A dermatoscopic image of a skin lesion.
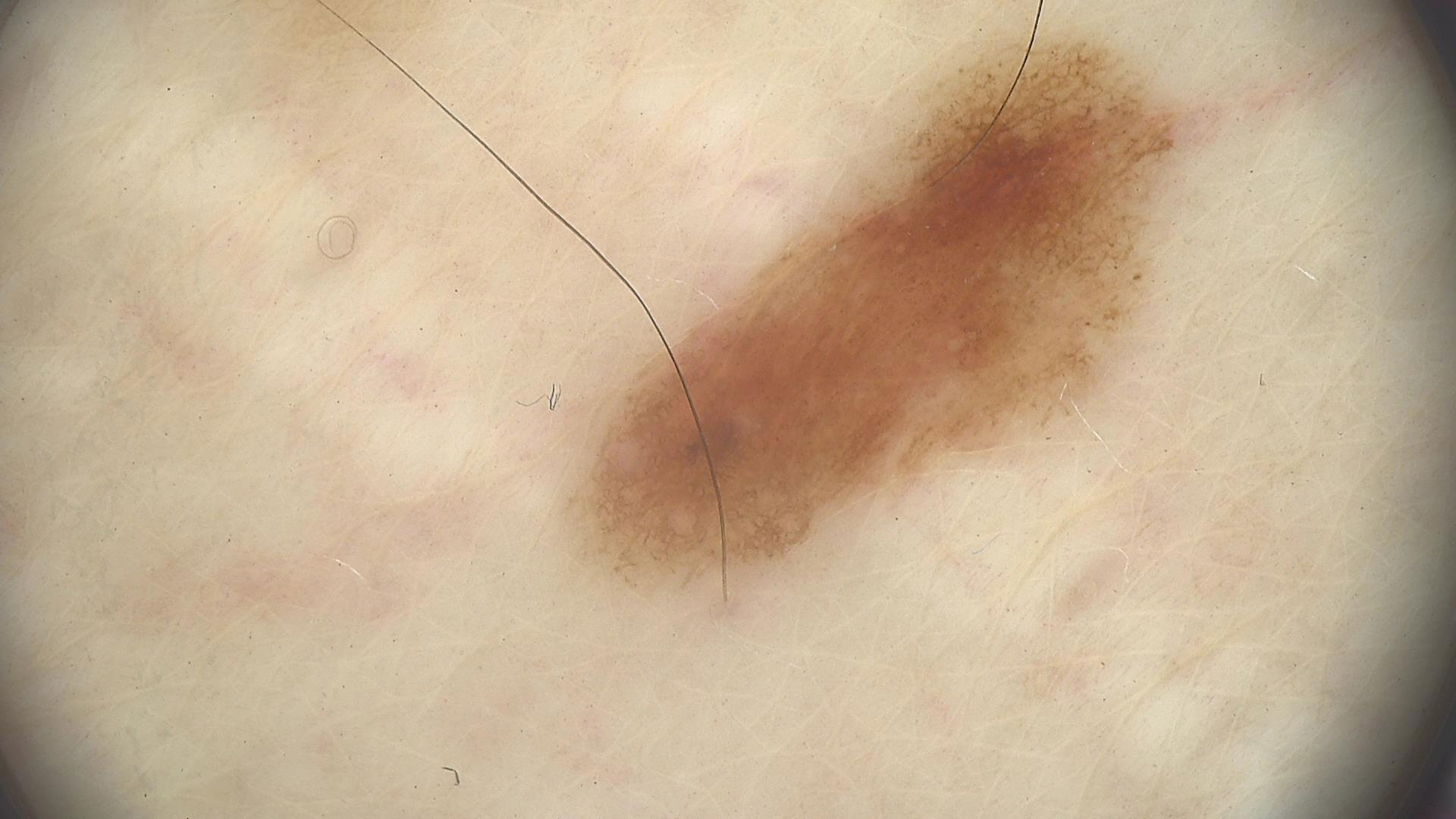Findings:
* diagnosis · dysplastic junctional nevus (expert consensus)